A dermoscopic close-up of a skin lesion: 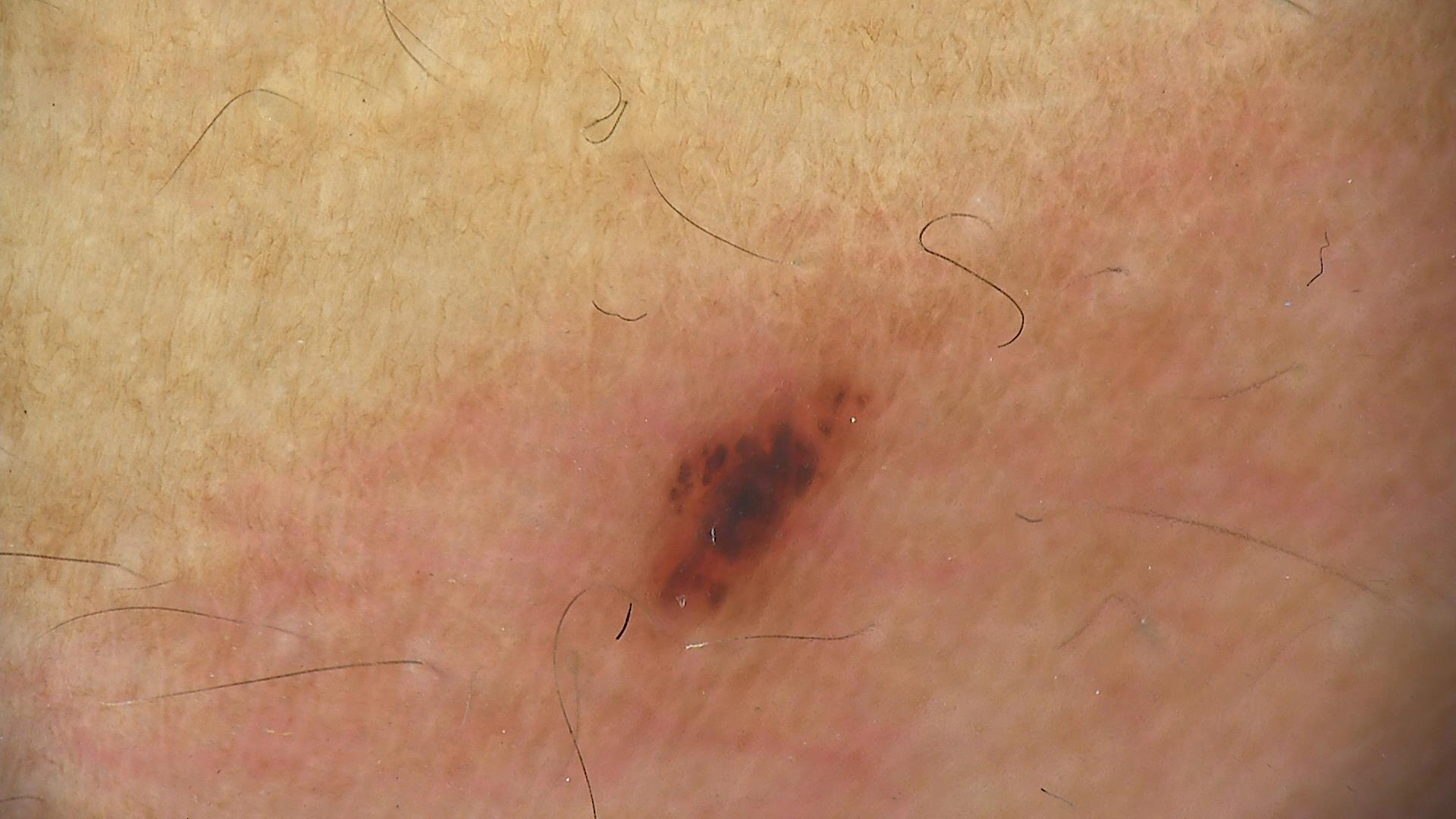Conclusion:
Diagnosed as a dysplastic junctional nevus.